Reported duration is less than one week; symptoms reported: itching; the affected area is the head or neck; the lesion is described as raised or bumpy; this image was taken at an angle:
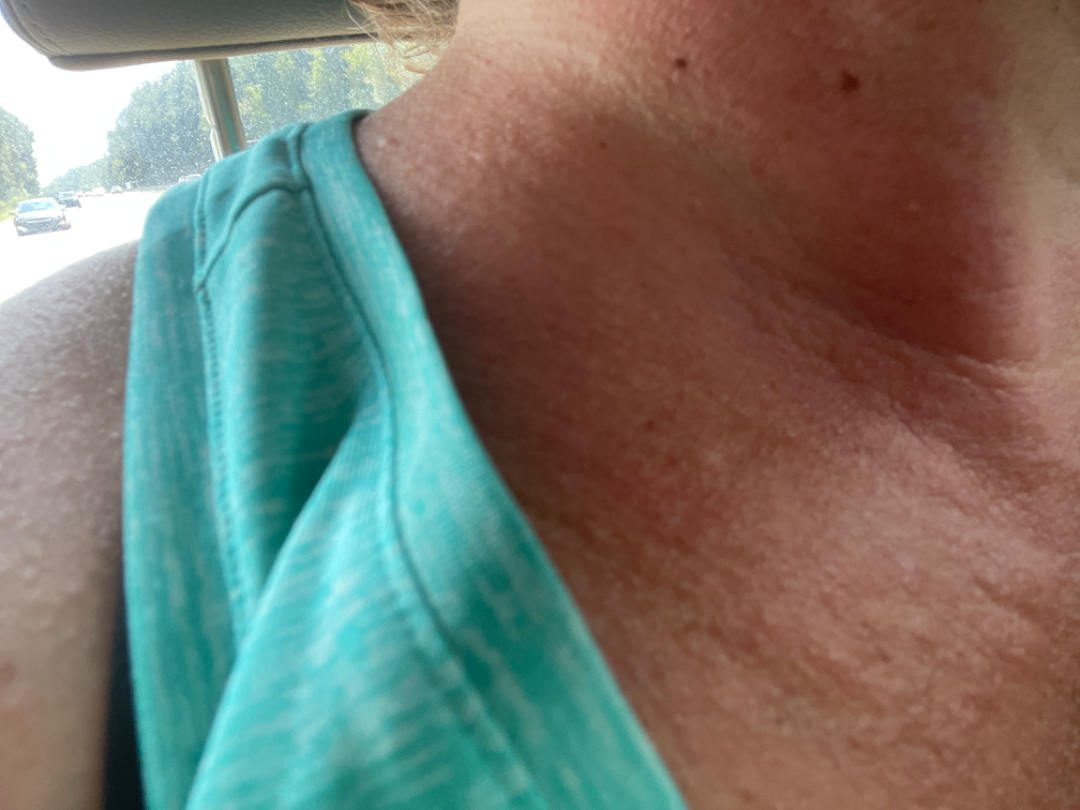| feature | finding |
|---|---|
| assessment | indeterminate |